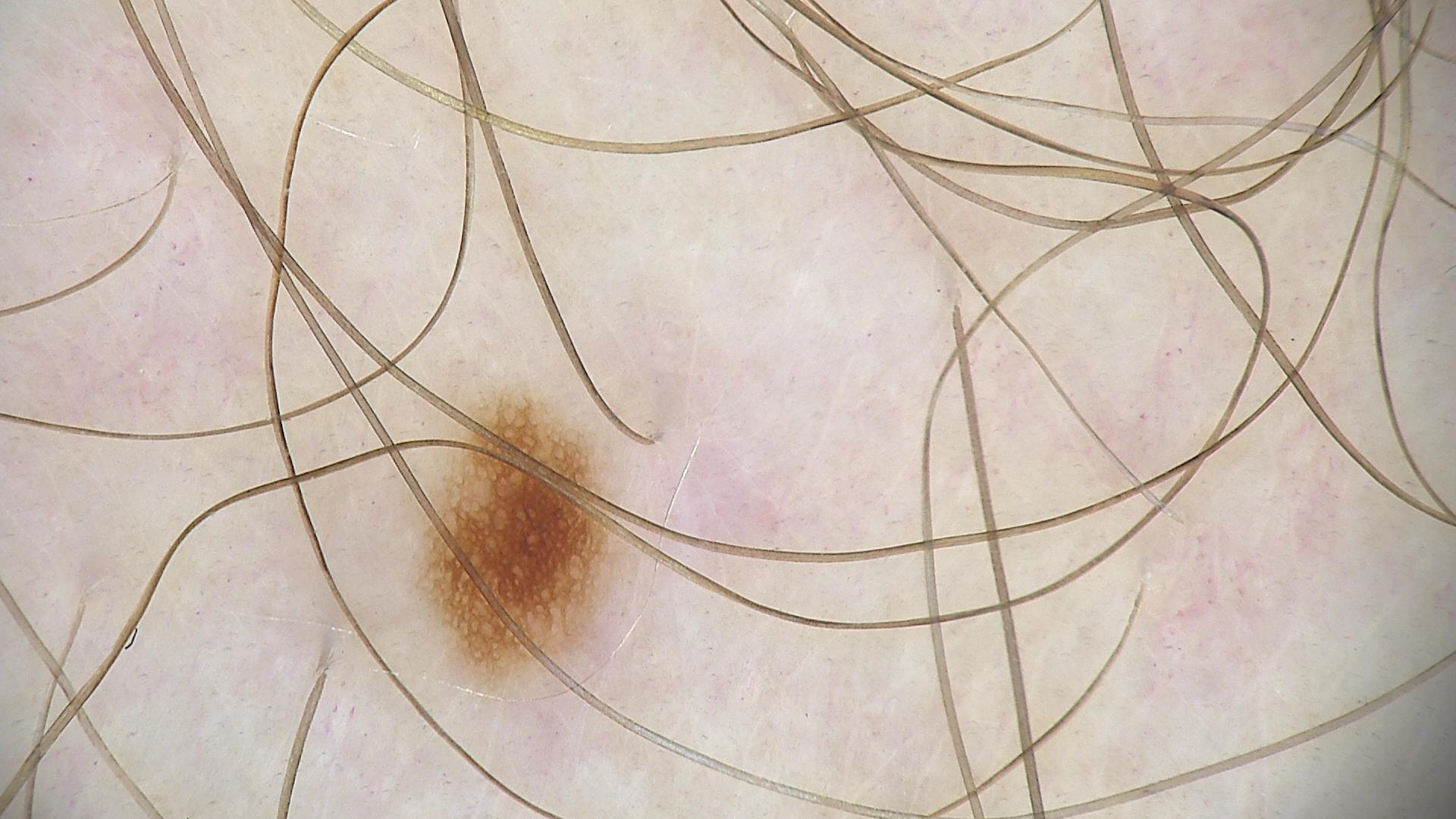Q: What is this lesion?
A: dysplastic junctional nevus (expert consensus)